A female subject in their mid- to late 50s; per the chart, no prior melanoma and no melanoma in first-degree relatives; the patient is FST IV; a dermatoscopic image of a skin lesion: 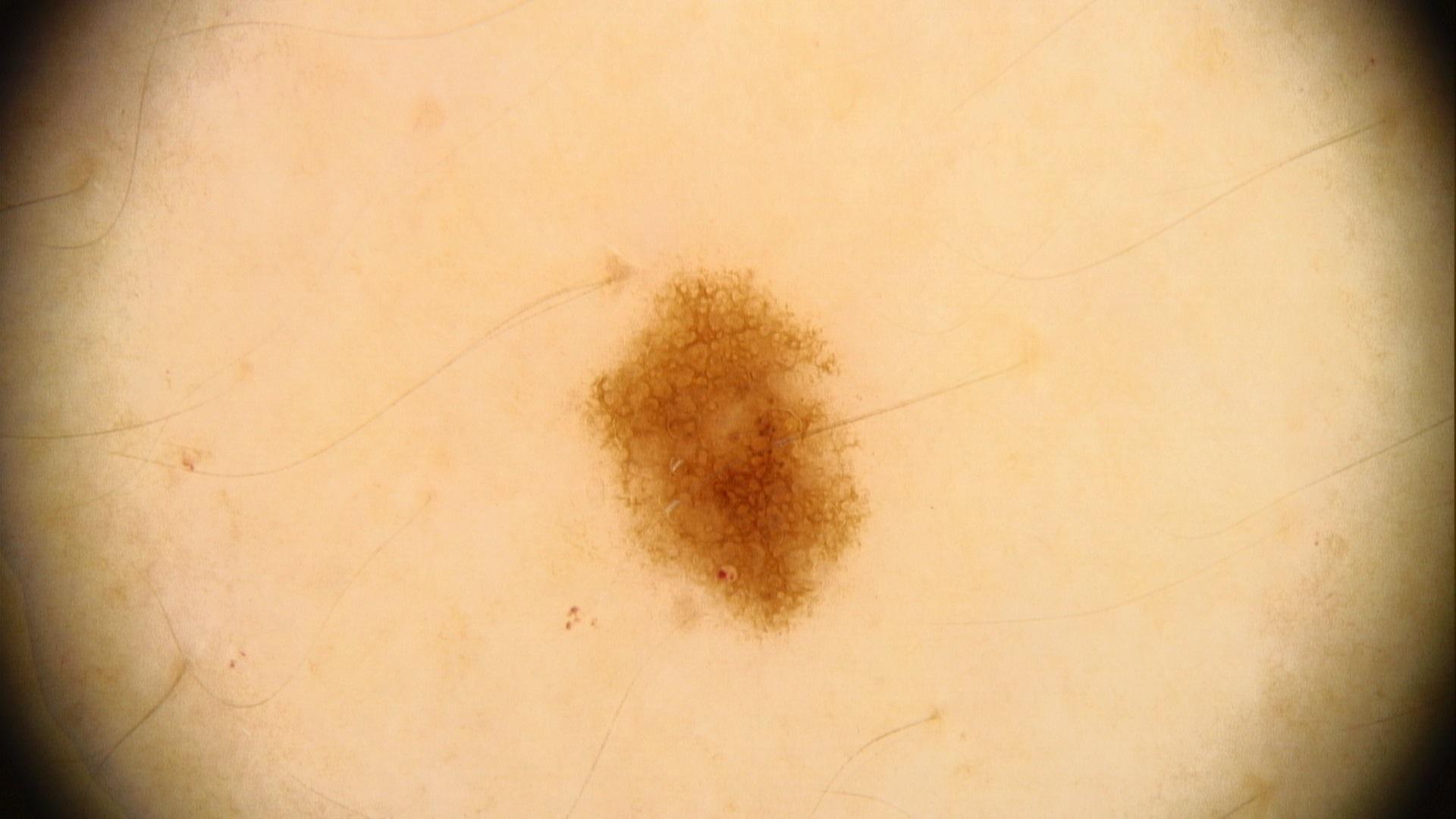The lesion was found on the trunk. The clinical impression was a benign lesion — a nevus.